The patient is 18–29, female. The affected area is the leg and arm. The photo was captured at a distance:
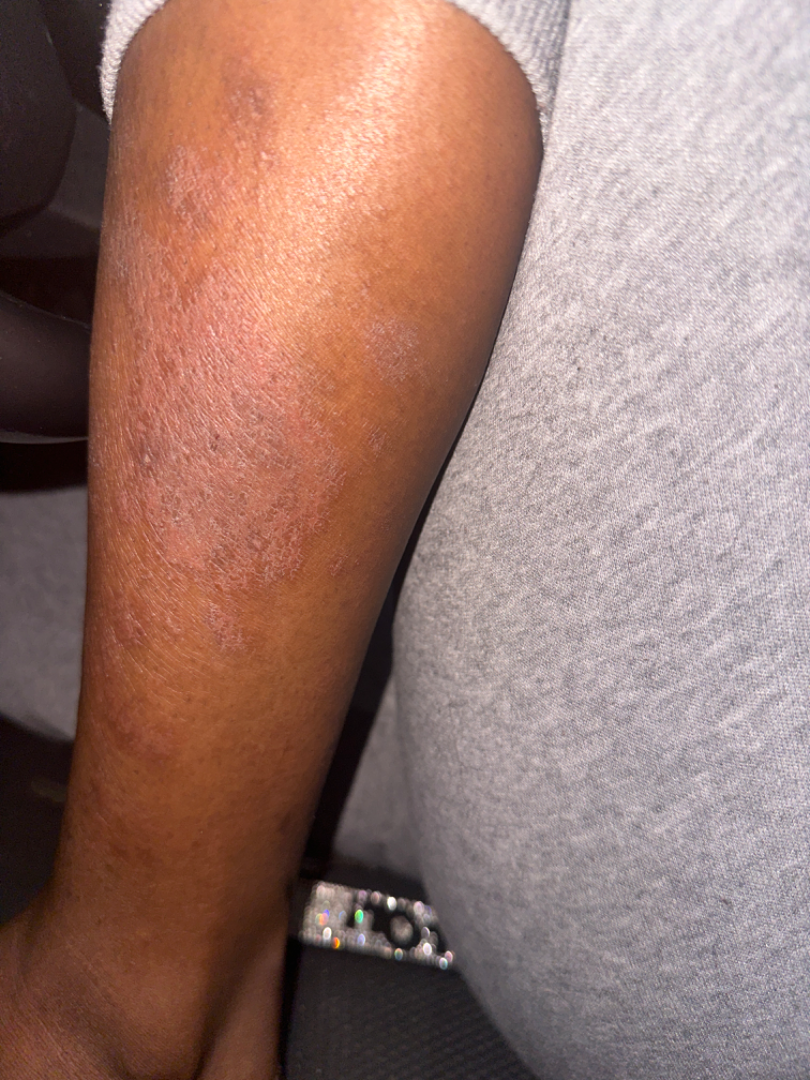Q: How does the lesion feel?
A: flat, raised or bumpy and rough or flaky
Q: When did this start?
A: one to three months
Q: What is the patient's skin tone?
A: Fitzpatrick phototype V; lay graders estimated Monk Skin Tone 6 or 7 (two reviewer pools)
Q: How does the patient describe it?
A: a rash
Q: What symptoms does the patient report?
A: darkening, enlargement, bothersome appearance, burning and itching
Q: What conditions are considered?
A: Psoriasis and Eczema were each considered, in no particular order